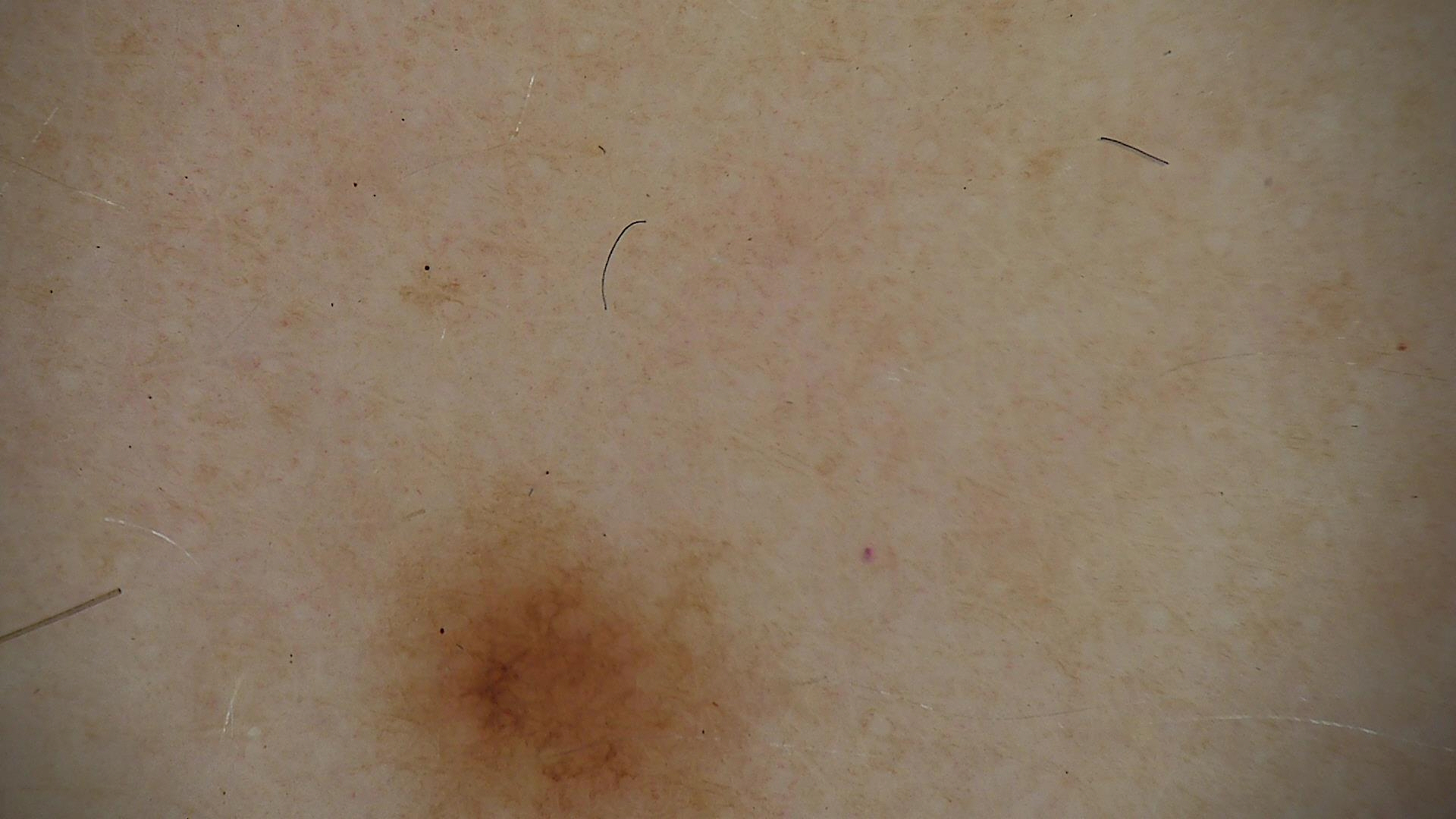imaging: dermatoscopy | class: dysplastic junctional nevus (expert consensus).